A skin lesion imaged with a dermatoscope.
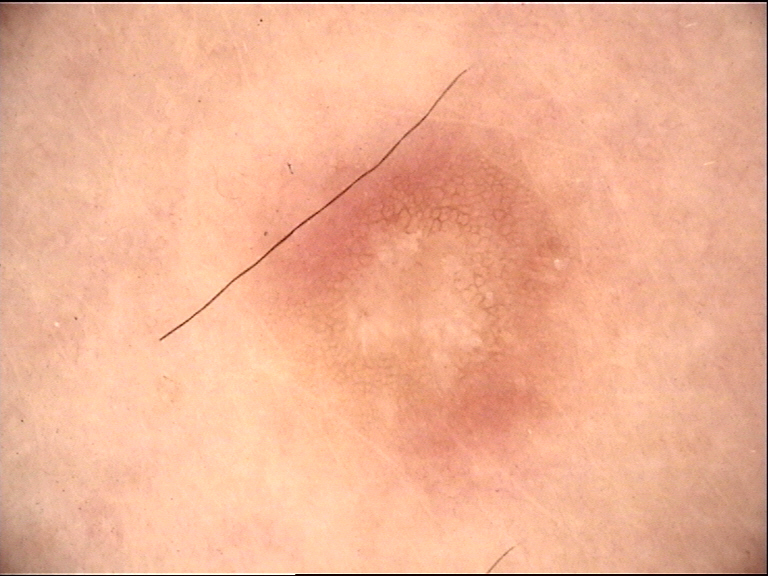* diagnostic label · dermatofibroma (expert consensus)